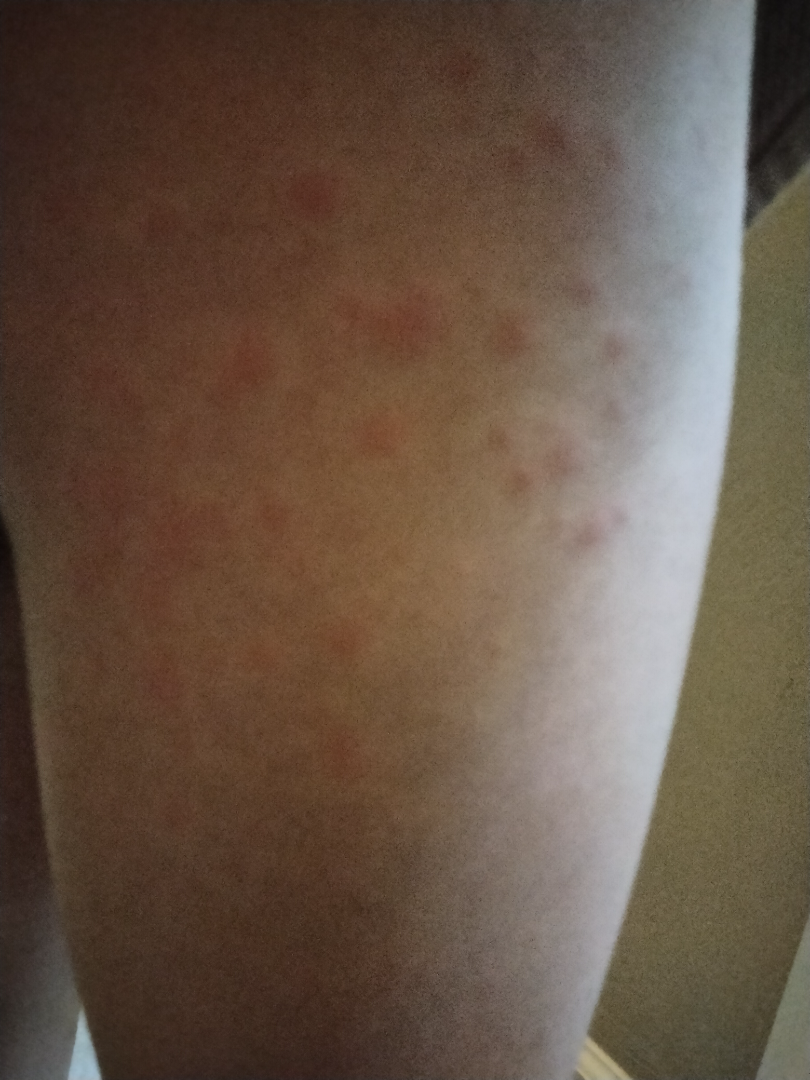The dermatologist could not determine a likely condition from the photograph alone.
The lesion involves the leg, palm, top or side of the foot and back of the hand.
A close-up photograph.